This image was taken at an angle, the contributor is a male aged 30–39, the lesion involves the arm:
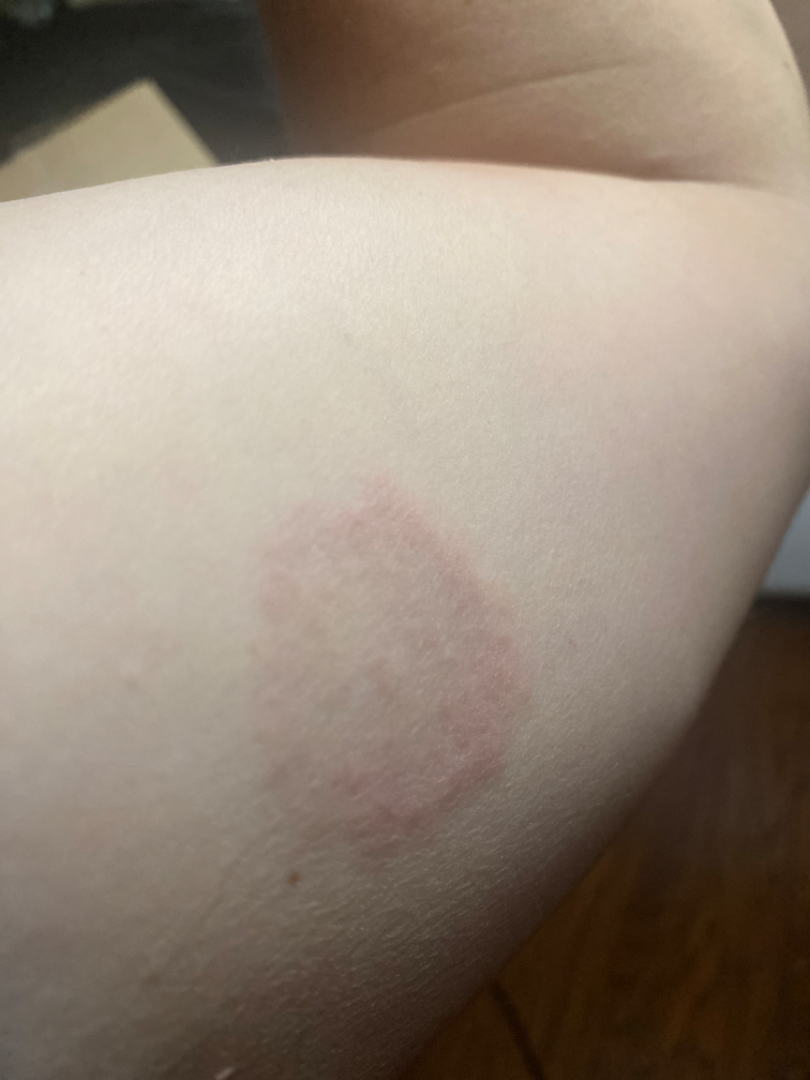| key | value |
|---|---|
| assessment | could not be assessed |